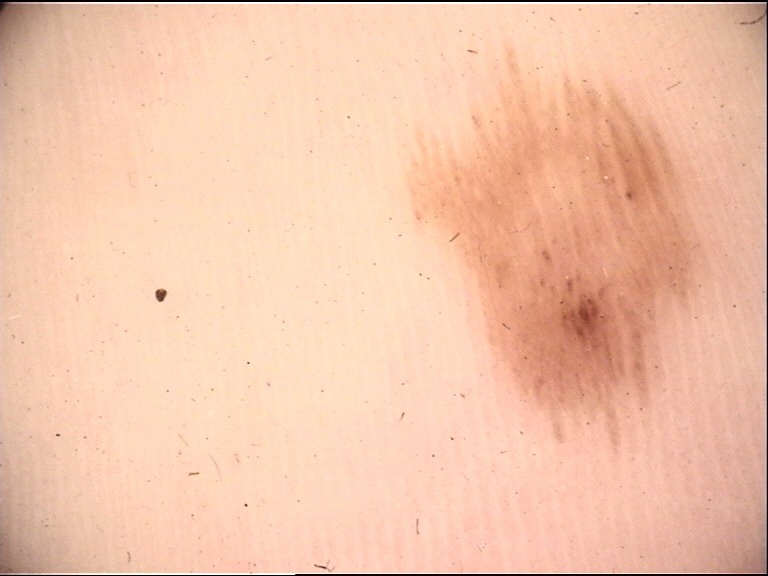A dermatoscopic image of a skin lesion.
This is a banal lesion.
Diagnosed as an acral junctional nevus.